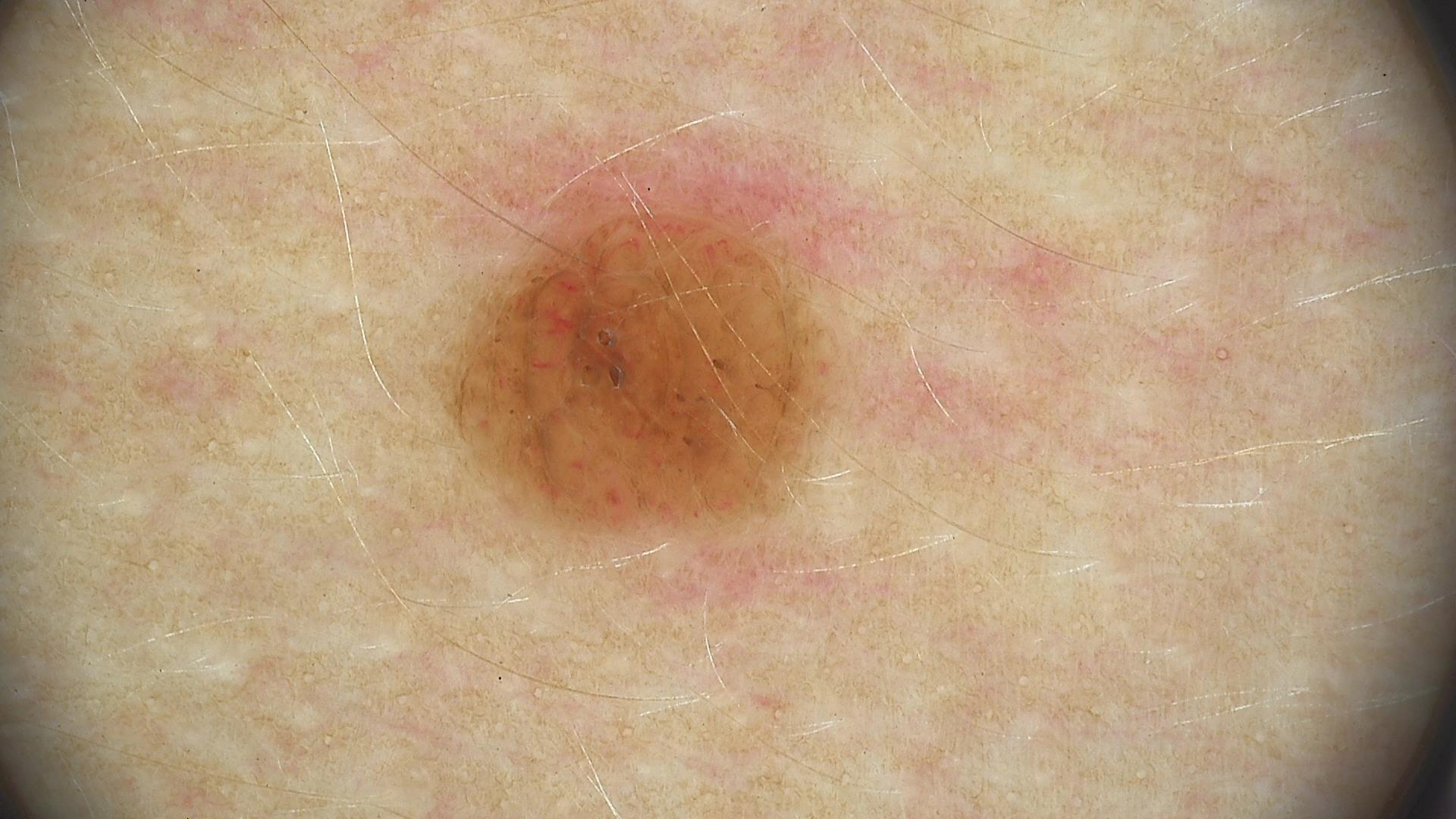<lesion>
  <diagnosis>
    <name>dermal nevus</name>
    <code>db</code>
    <malignancy>benign</malignancy>
    <super_class>melanocytic</super_class>
    <confirmation>expert consensus</confirmation>
  </diagnosis>
</lesion>